A dermoscopic photograph of a skin lesion: 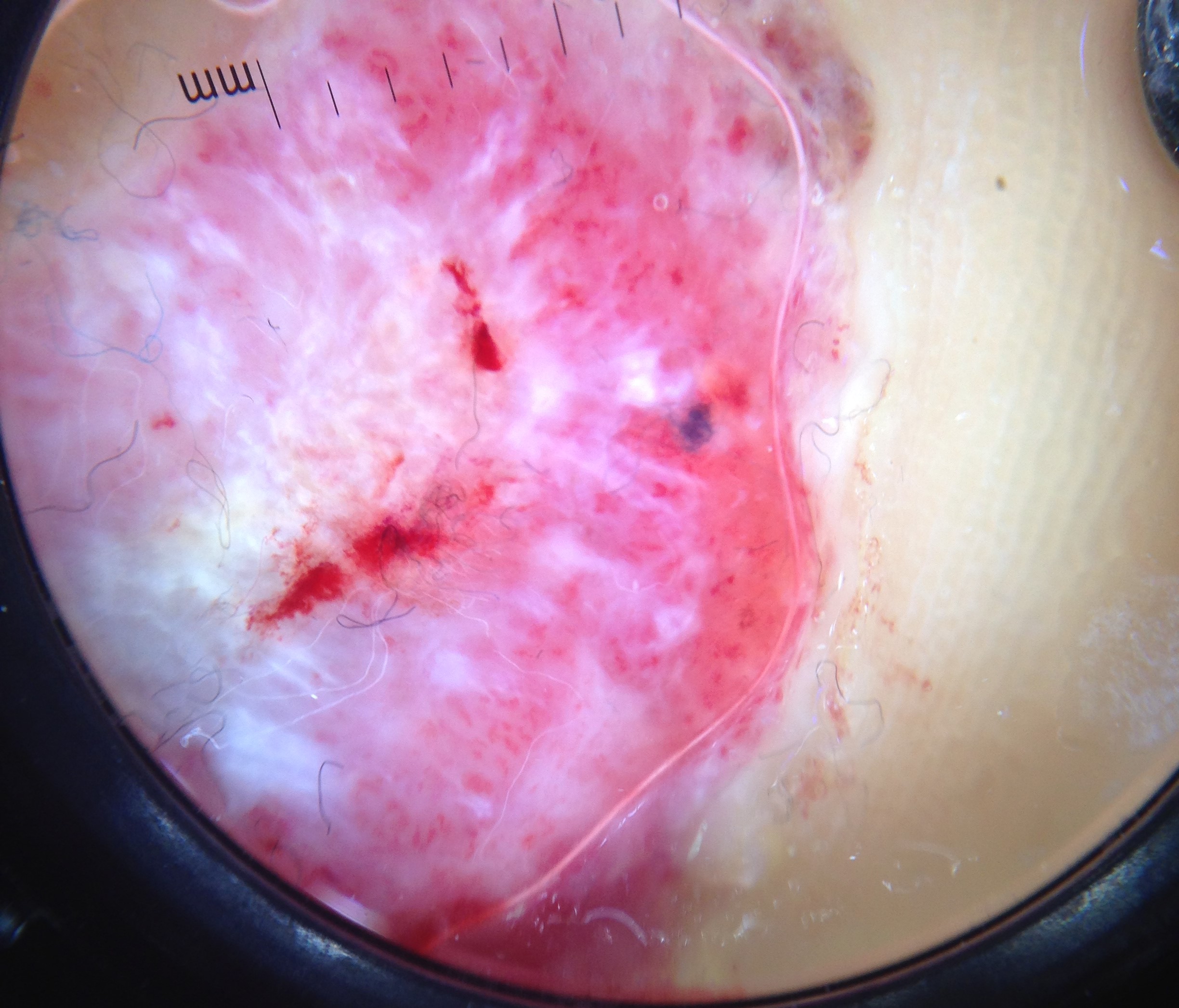pathology = acral nodular melanoma (biopsy-proven).